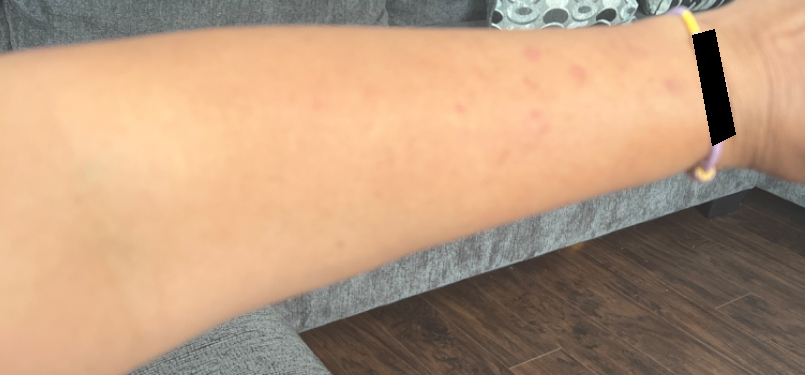Case summary:
- image framing · at a distance
- lesion texture · raised or bumpy and rough or flaky
- affected area · arm
- patient-reported symptoms · darkening, enlargement, itching and bothersome appearance
- subject · female
- self-categorized as · a rash
- associated systemic symptoms · joint pain, fatigue, shortness of breath and chills
- onset · three to twelve months
- diagnostic considerations · Prurigo nodularis (favored)